The photograph is a close-up of the affected area. Female contributor, age 30–39. Located on the arm.
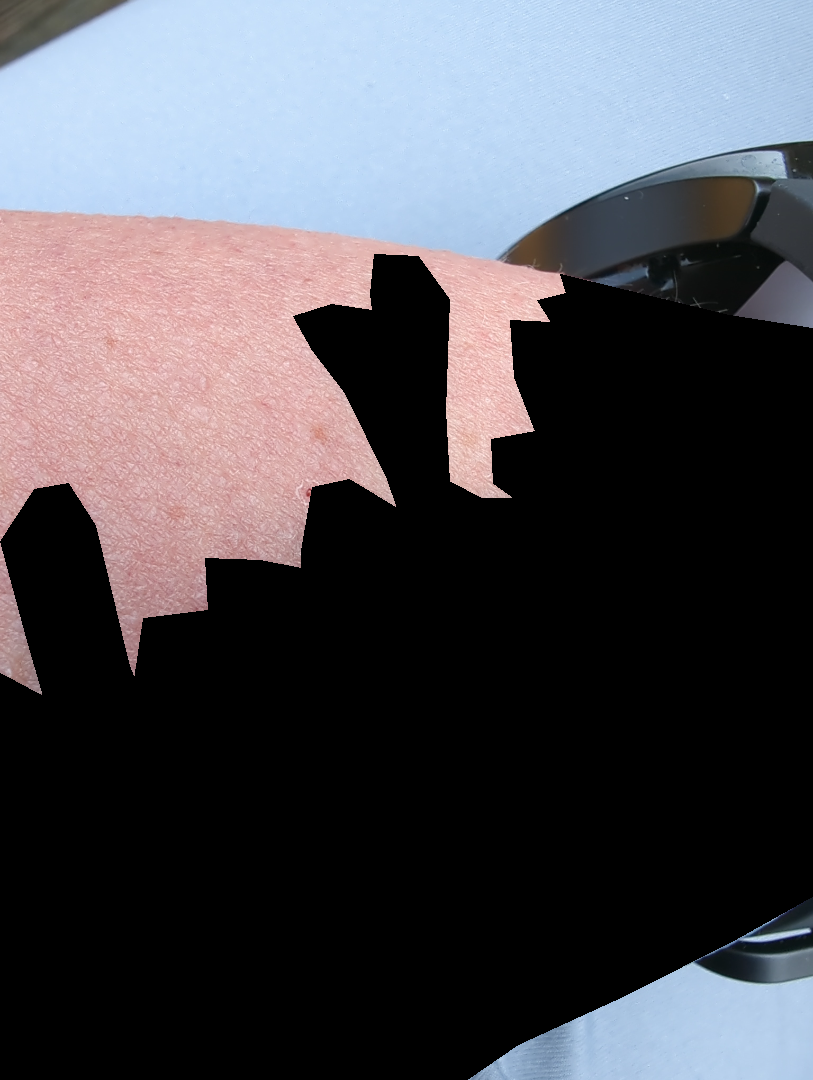The skin condition could not be confidently assessed from this image.